A male patient 62 years old; the patient says their skin reddens with sun exposure; a dermoscopic image of a skin lesion:
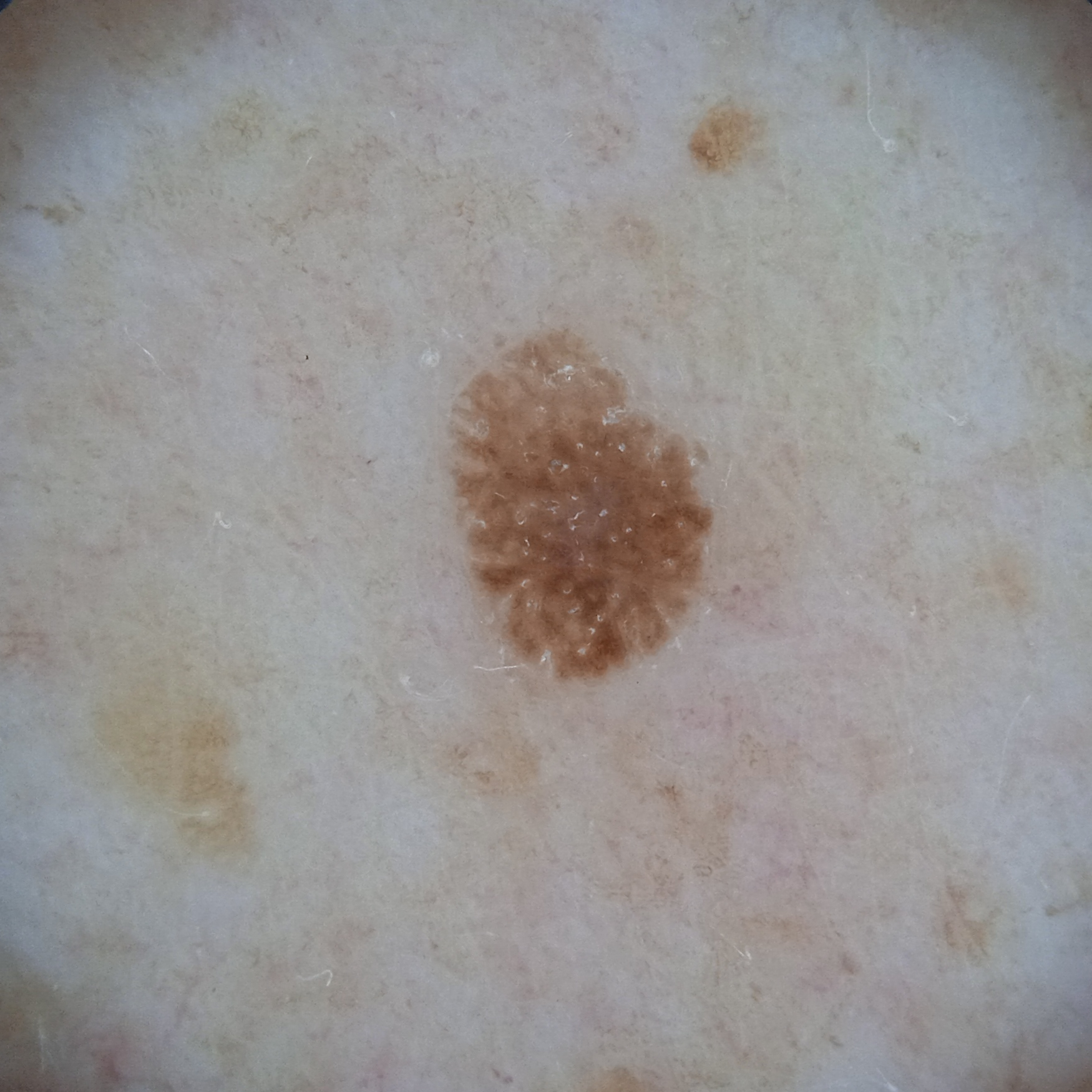Case:
- location · the back
- size · 4.3 mm
- assessment · seborrheic keratosis (dermatologist consensus)